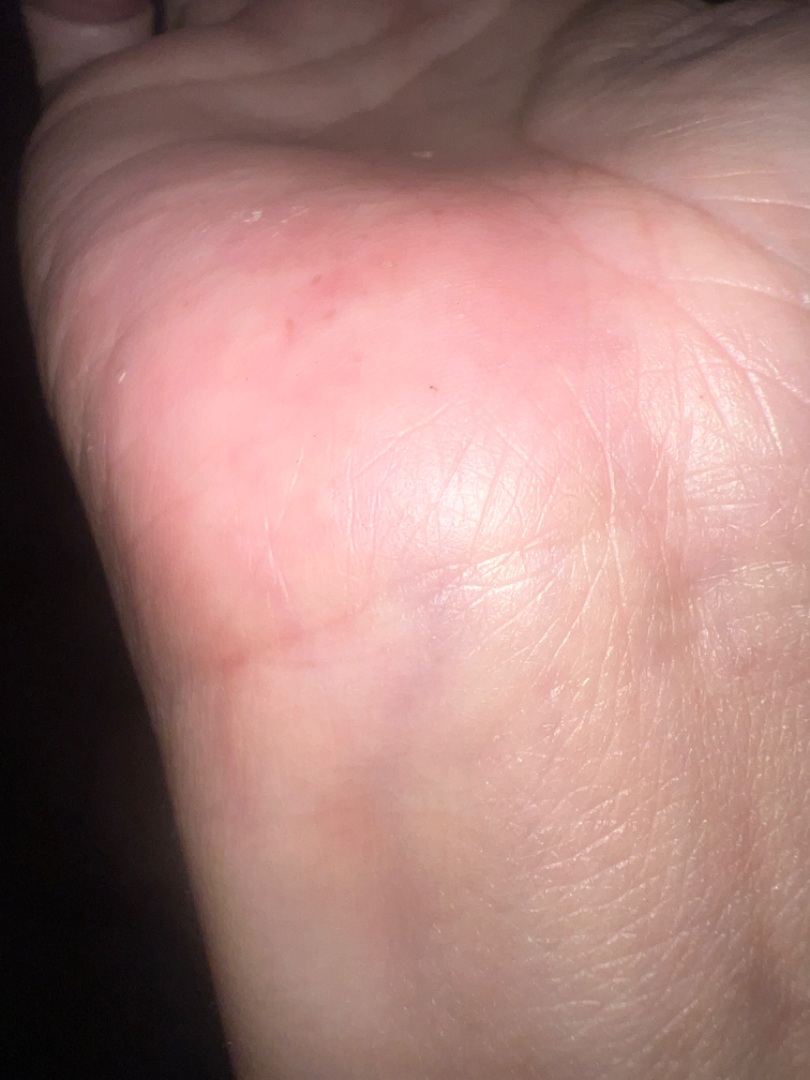view — at an angle
location — palm
patient's own categorization — a rash
patient — female, age 40–49
systemic symptoms — none reported
surface texture — raised or bumpy
symptom duration — one to four weeks
reported symptoms — itching
clinical impression — the leading consideration is Eczema; also on the differential is Allergic Contact Dermatitis